A close-up photograph; the affected area is the arm, front of the torso and leg.
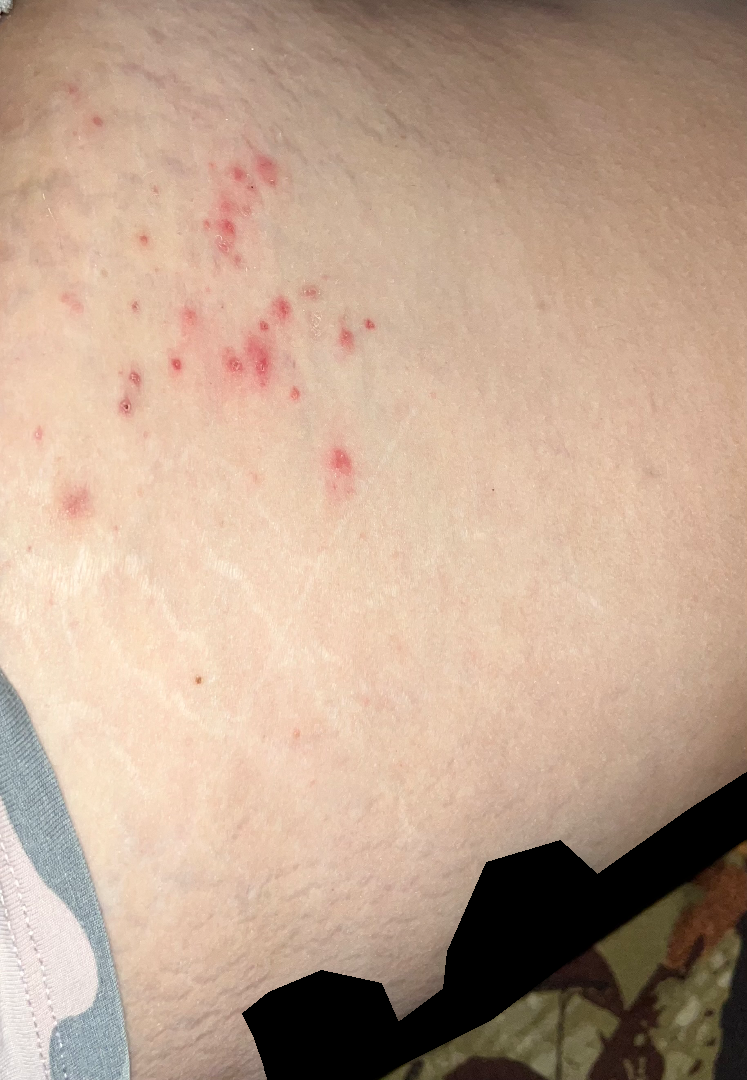Q: What was the assessment?
A: could not be assessed
Q: What is the patient's skin tone?
A: Fitzpatrick III; lay reviewers estimated 2 on the MST
Q: Texture?
A: raised or bumpy
Q: Duration?
A: one to four weeks